A dermoscopic image of a skin lesion.
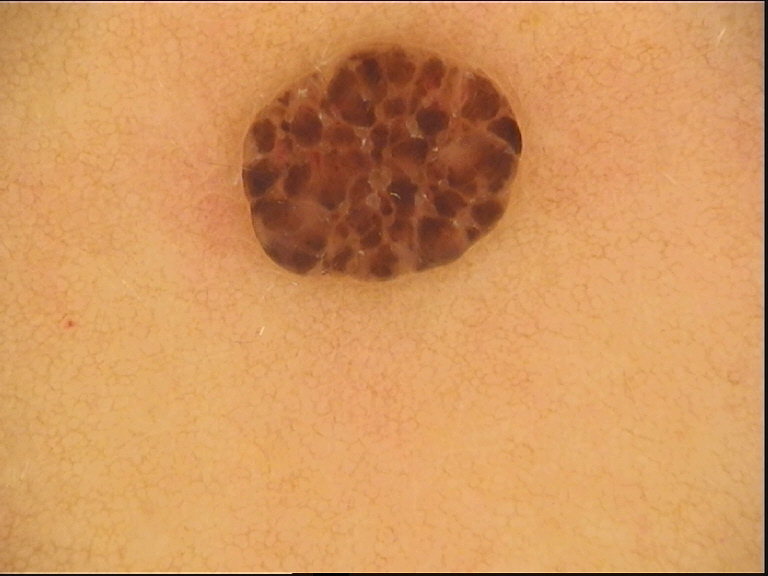Q: What was the diagnostic impression?
A: dermal nevus (expert consensus)